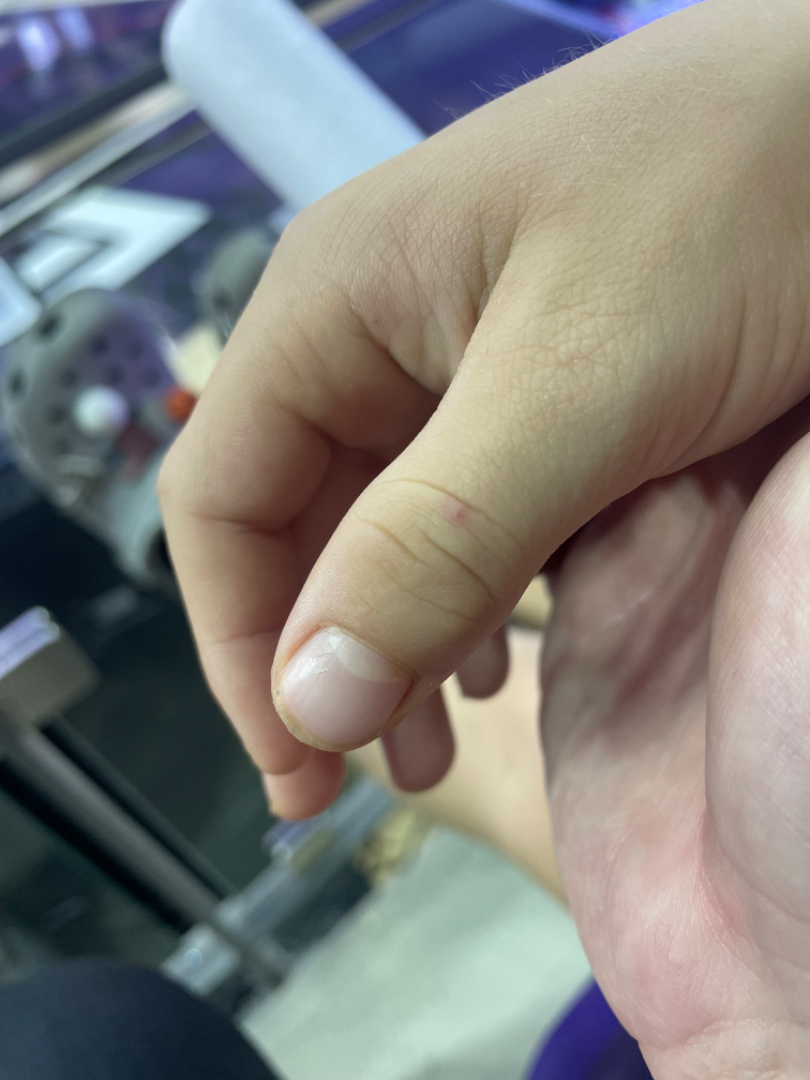Patient information: The arm is involved. An image taken at an angle. Review: On dermatologist assessment of the image: Insect Bite (considered); Molluscum Contagiosum (considered).